A dermoscopic photograph of a skin lesion.
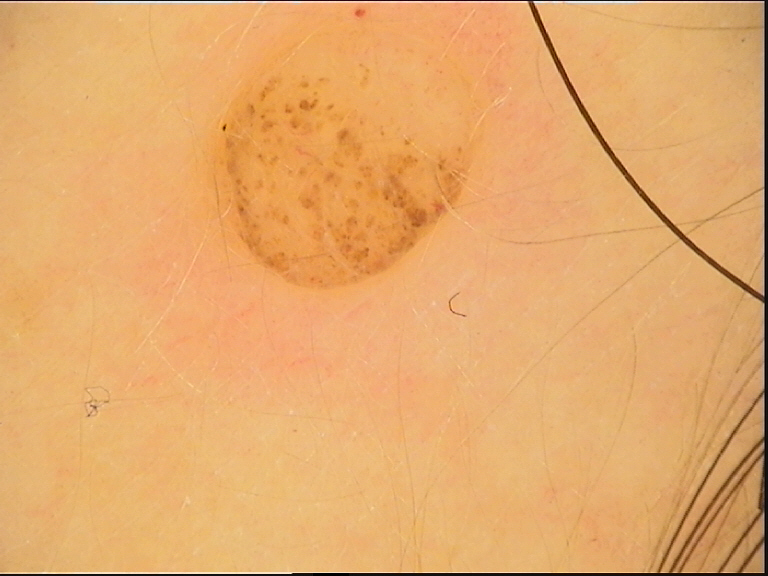The morphology is that of a banal lesion. Classified as a dermal nevus.